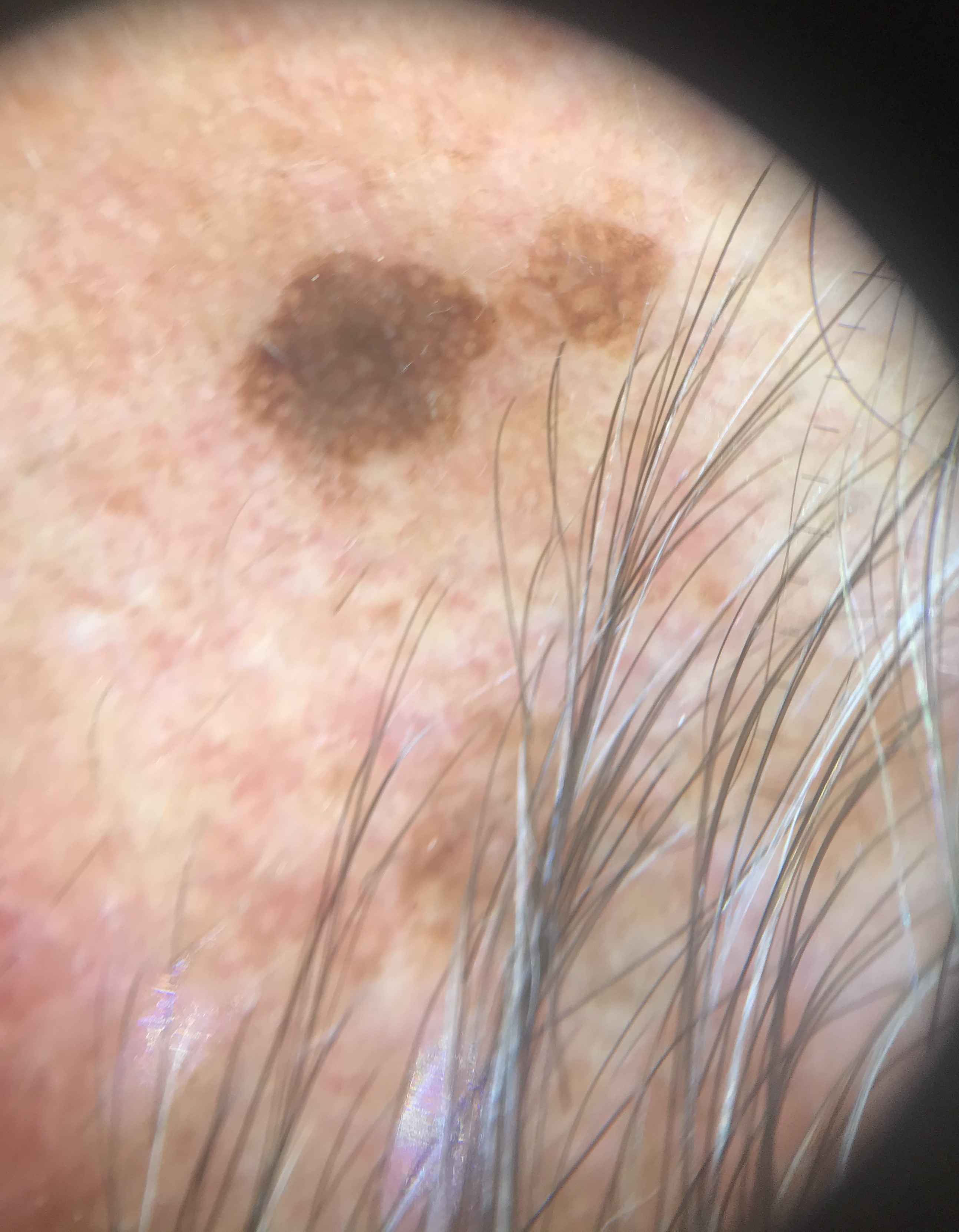{
  "diagnosis": {
    "name": "seborrheic keratosis",
    "code": "sk",
    "malignancy": "benign",
    "super_class": "non-melanocytic",
    "confirmation": "expert consensus"
  }
}